The contributor is male, close-up view, located on the leg and front of the torso — 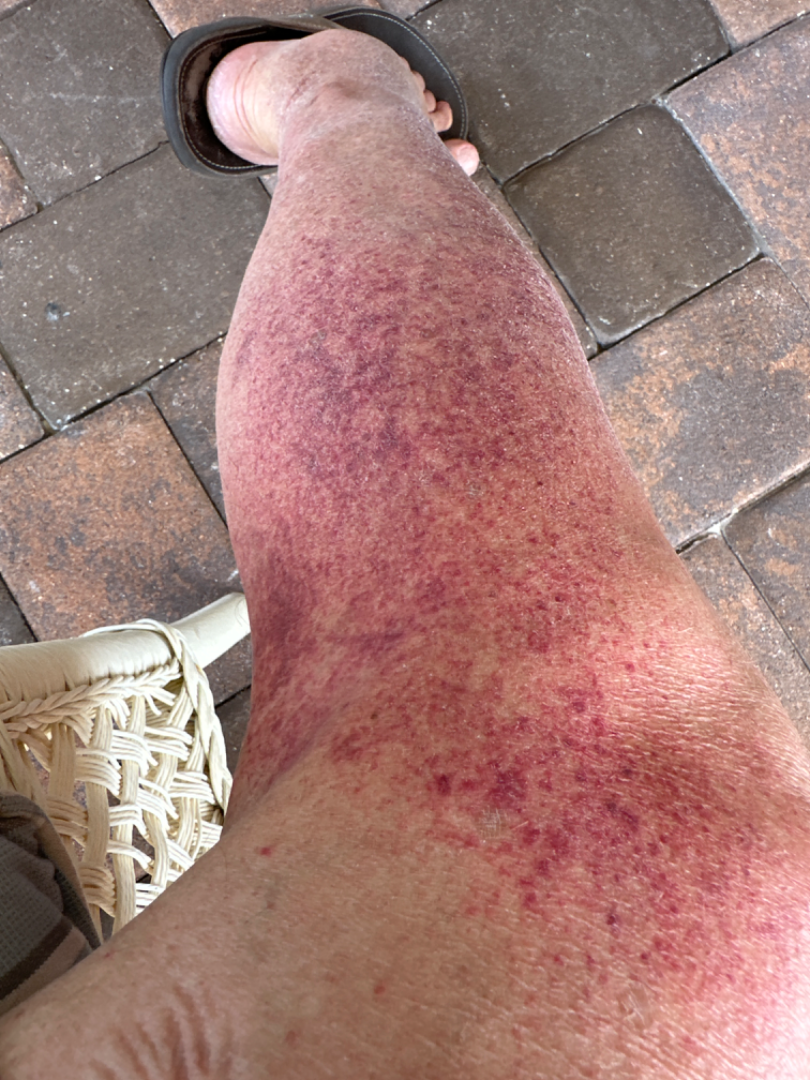described texture: flat, self-categorized as: a rash, lesion symptoms: bothersome appearance and enlargement, differential diagnosis: the impression is Leukocytoclastic Vasculitis.